This is a dermoscopic photograph of a skin lesion; a male subject aged approximately 85 or older — 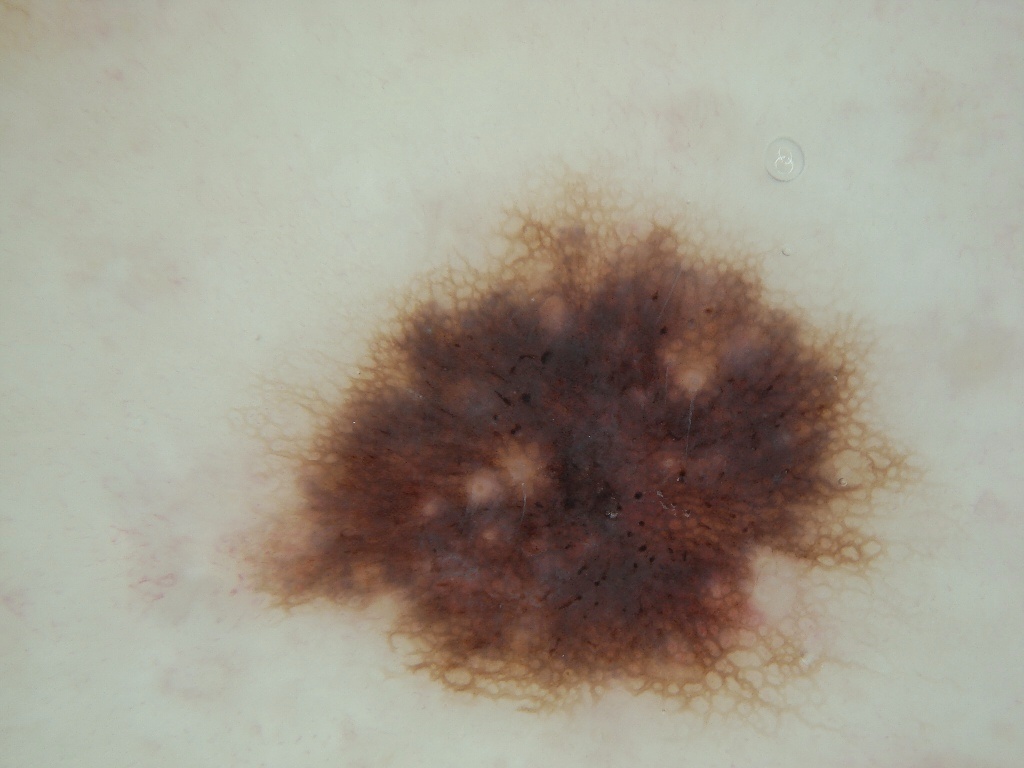Dermoscopic review identifies pigment network and milia-like cysts.
The lesion covers approximately 30% of the dermoscopic field.
With coordinates (x1, y1, x2, y2), the visible lesion spans 226 190 920 713.
Expert review diagnosed this as a melanocytic nevus, a benign skin lesion.